A dermoscopic view of a skin lesion:
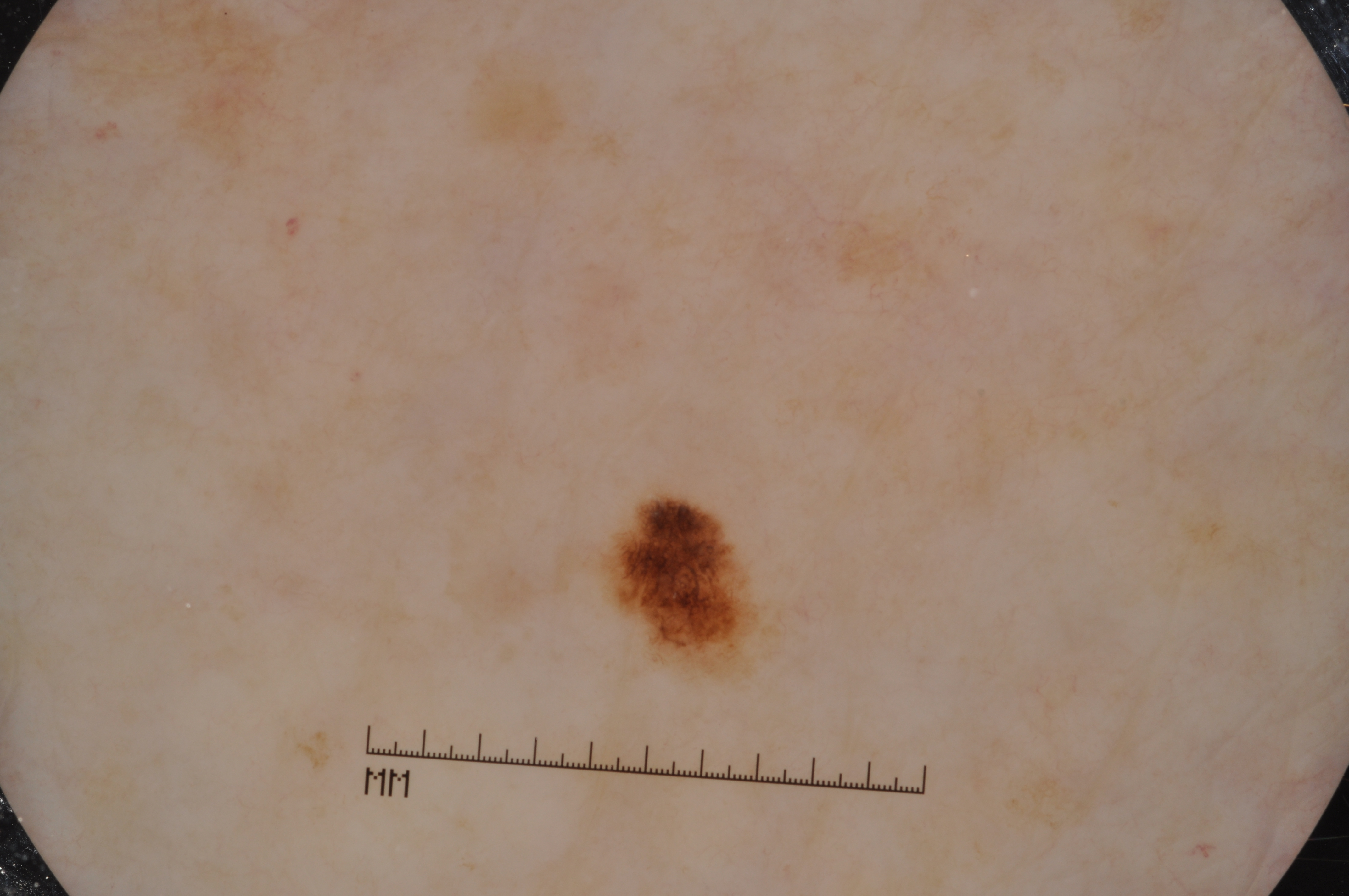As (left, top, right, bottom), the lesion spans 595 488 760 678. Dermoscopy demonstrates pigment network. The lesion takes up about 2% of the image. The lesion was assessed as a melanocytic nevus, a benign lesion.